A dermoscopic image of a skin lesion.
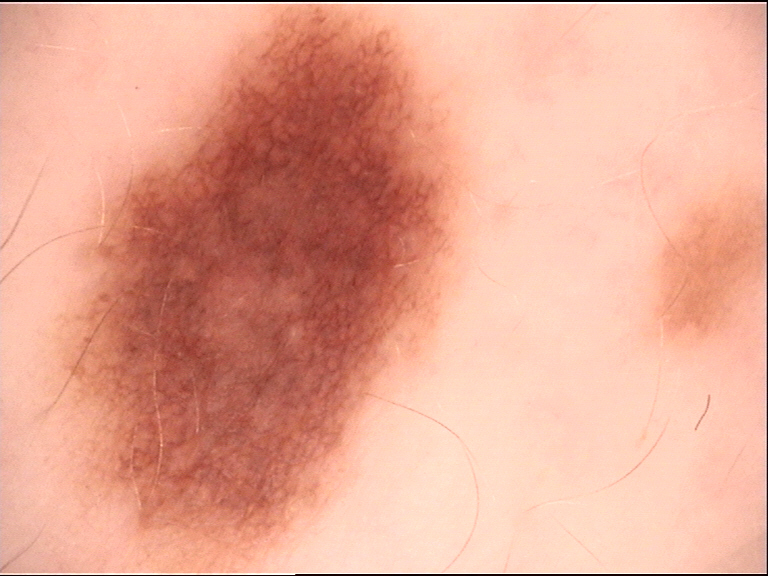Conclusion:
Labeled as a benign lesion — a dysplastic compound nevus.